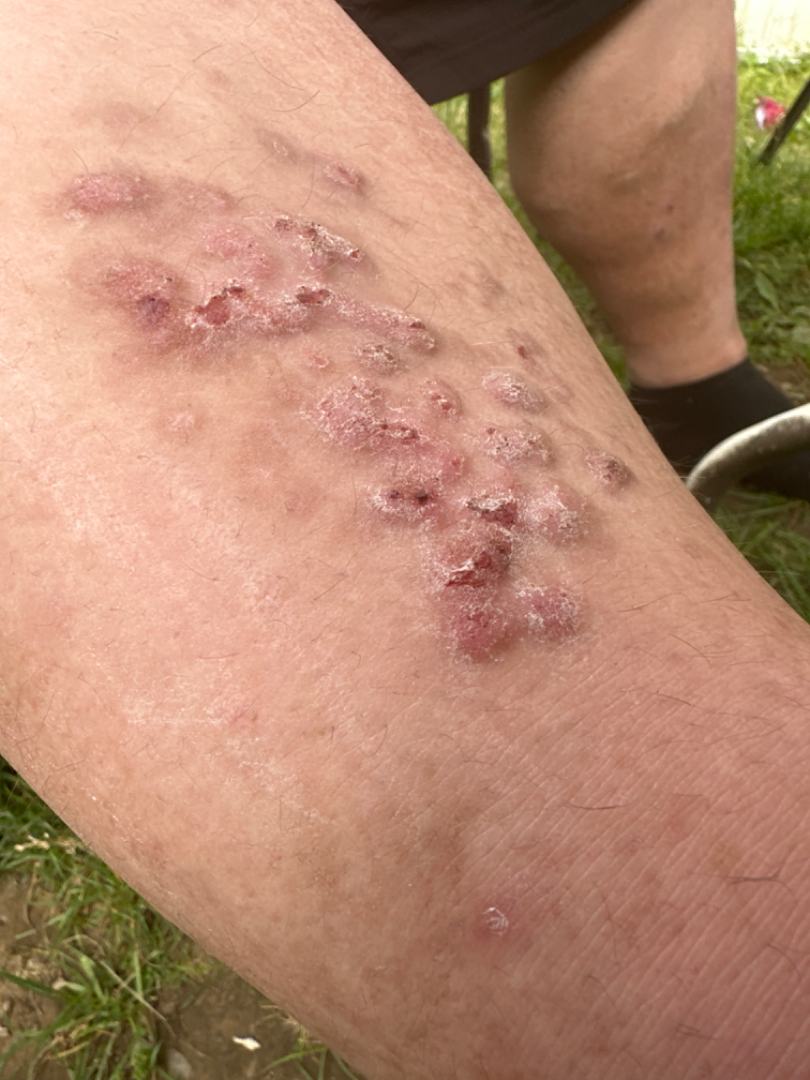Impression:
The primary impression is Psoriasis; also consider Prurigo nodularis.